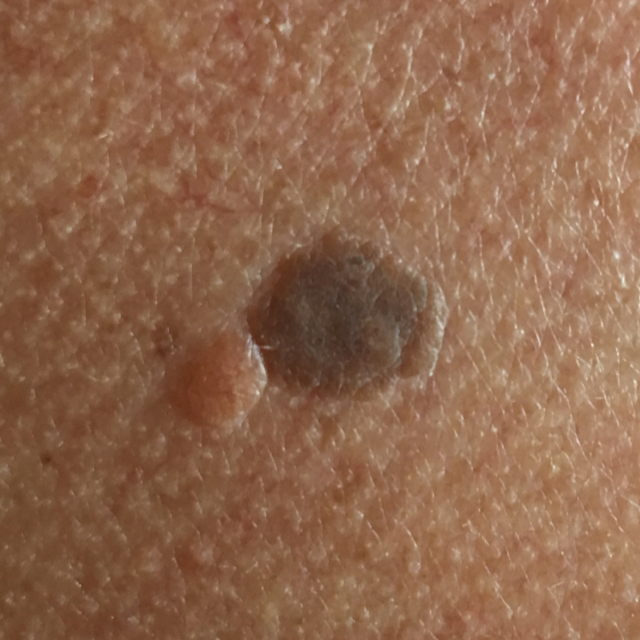image = clinical photo
anatomic site = the chest
patient-reported symptoms = elevation
assessment = seborrheic keratosis (clinical consensus)